The contributor is a male aged 50–59; the leg is involved; the patient described the issue as skin that appeared healthy to them; reported lesion symptoms include bothersome appearance; the photograph is a close-up of the affected area: 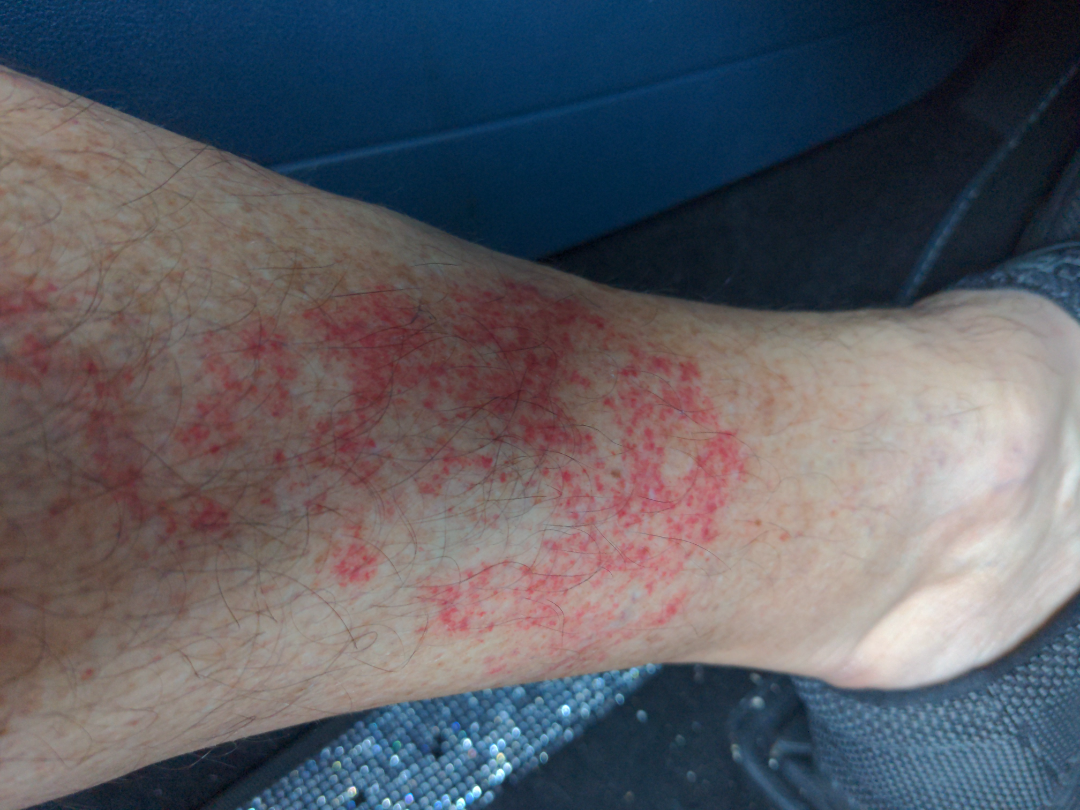<report>
  <assessment>ungradable on photographic review</assessment>
</report>